A male patient aged 38-42; a contact-polarized dermoscopy image of a skin lesion: 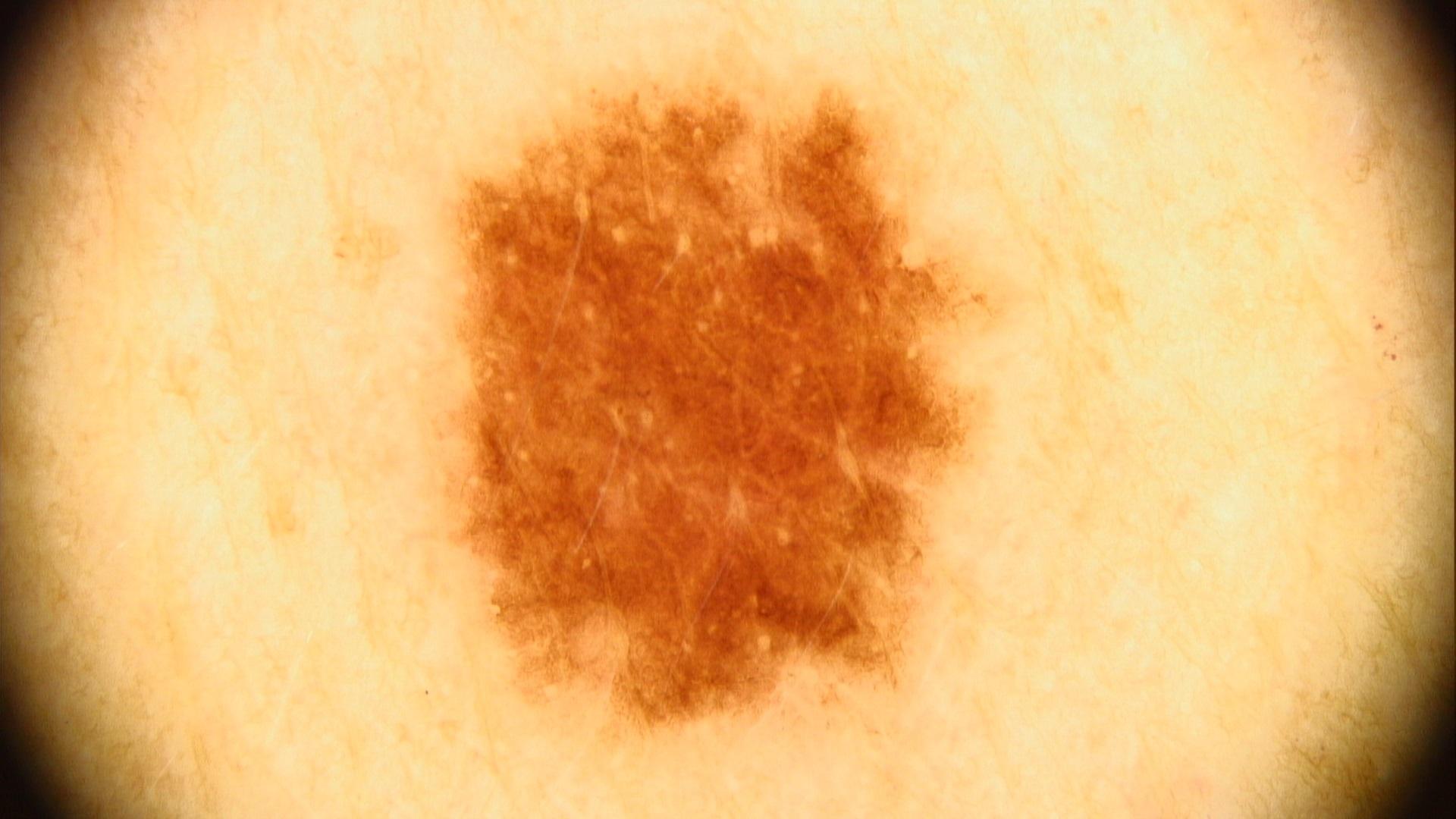site — the trunk; diagnostic label — Nevus (clinical impression).